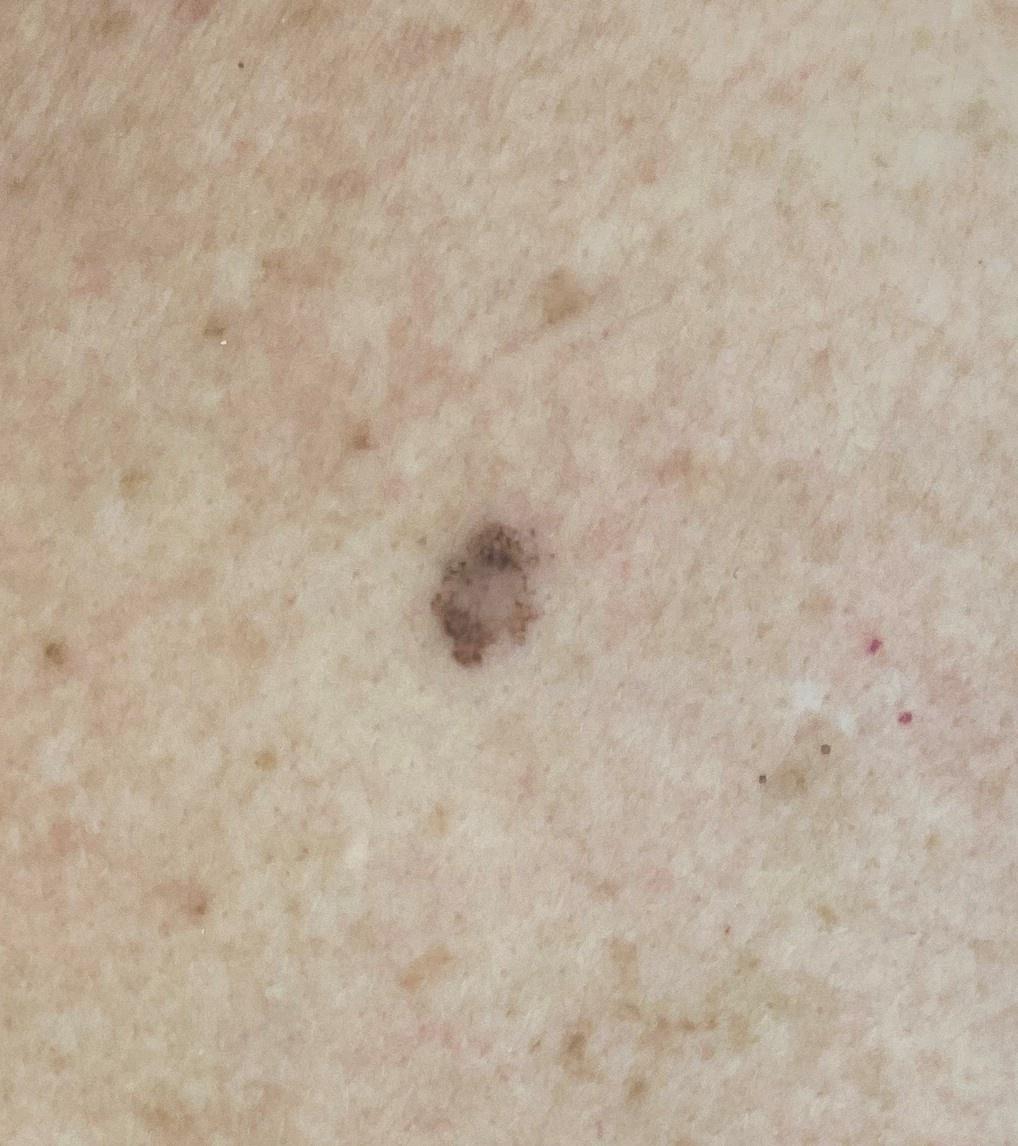location = the trunk (the posterior trunk) | pathology = Melanoma (biopsy-proven).